A female subject 48 years old · the patient describes having few moles overall · by self-report, a family history of skin cancer, a history of sunbed use, and no prior organ transplant · referred for assessment of suspected basal cell carcinoma · the patient says their skin reddens painfully with sun exposure · a clinical photograph showing a skin lesion.
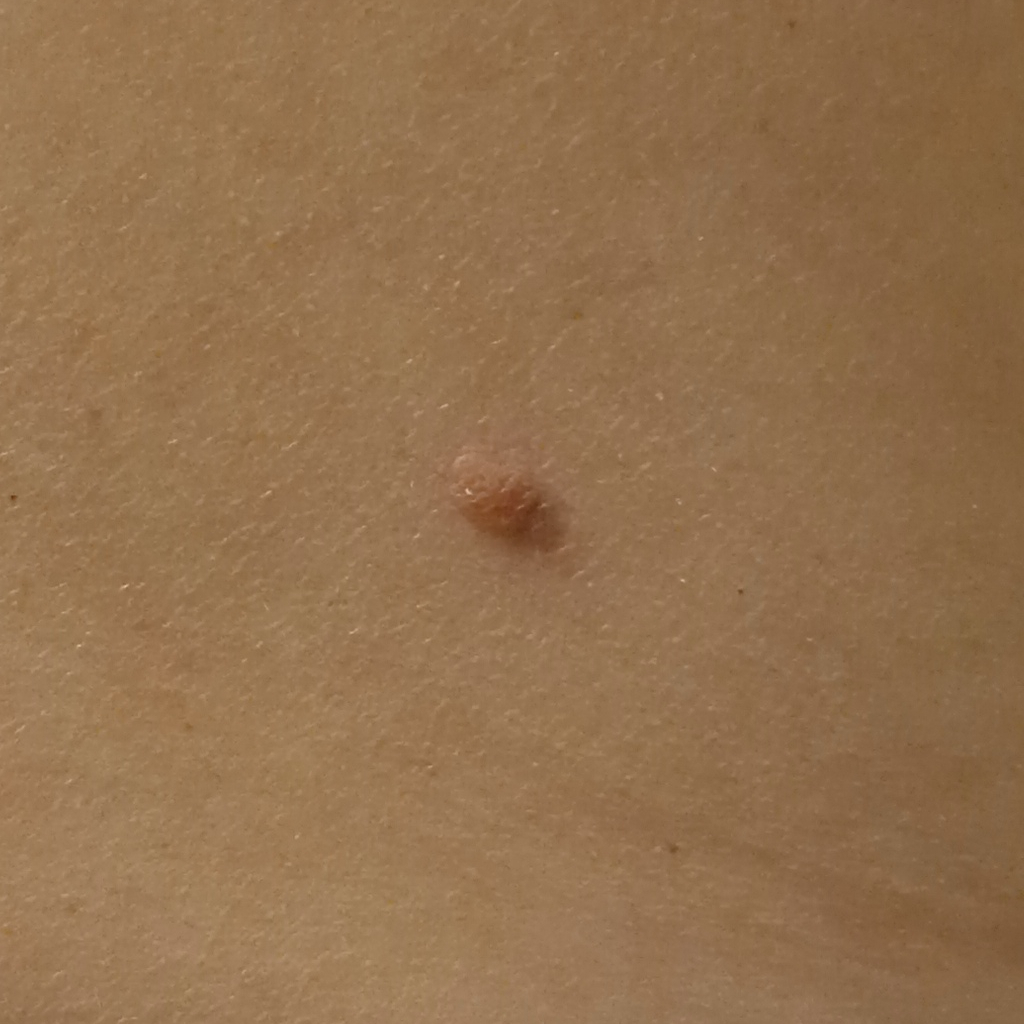<record>
<lesion_location>the back</lesion_location>
<lesion_size>
<diameter_mm>12.3</diameter_mm>
</lesion_size>
<diagnosis>
<name>basal cell carcinoma</name>
<malignancy>malignant</malignancy>
<procedure>excision</procedure>
<tumor_thickness_mm>1.1</tumor_thickness_mm>
</diagnosis>
</record>